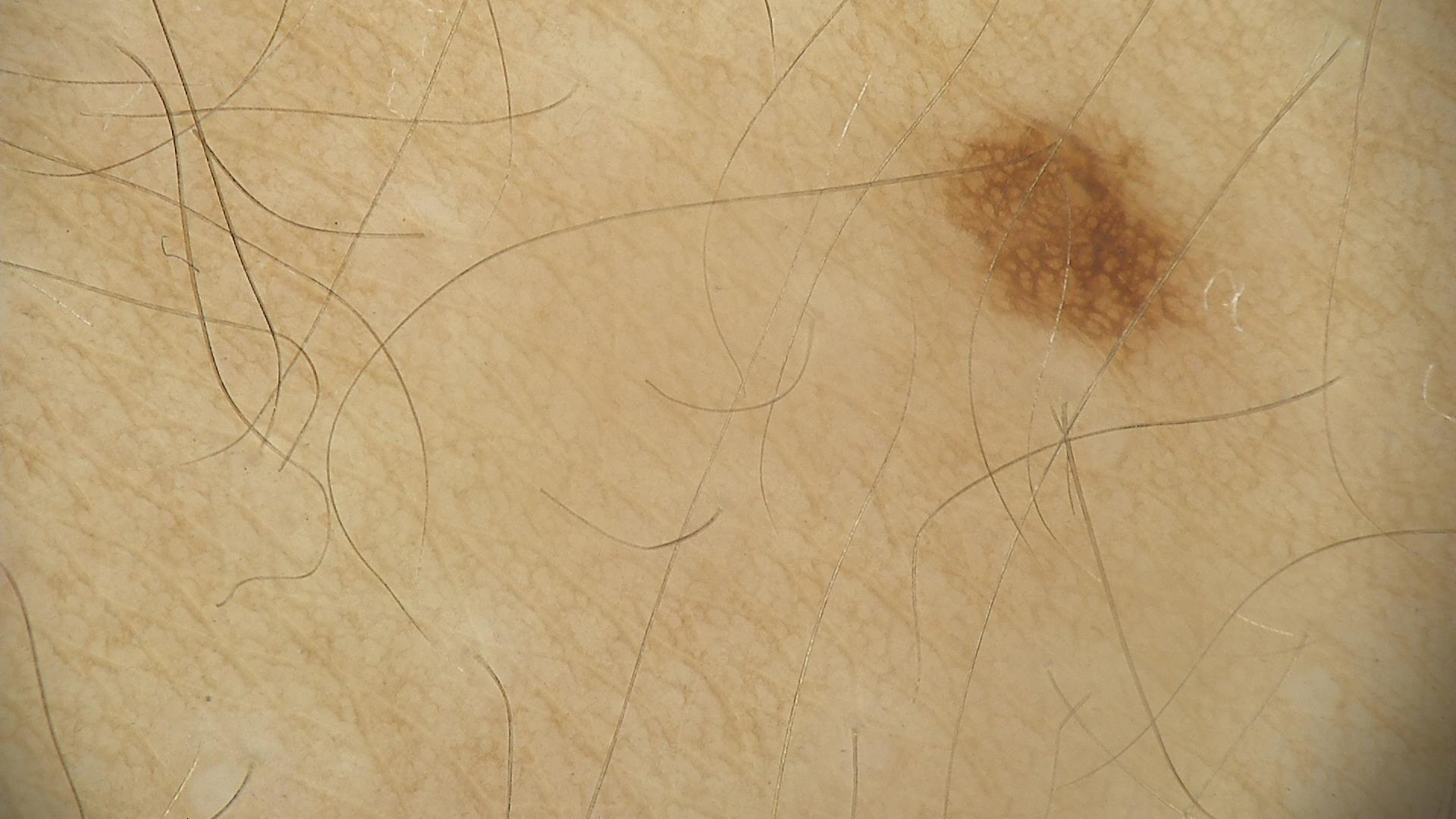class: dysplastic junctional nevus (expert consensus)